Located on the arm, no associated systemic symptoms reported, Fitzpatrick phototype III, the patient considered this a rash, the contributor is male, the photograph was taken at an angle.
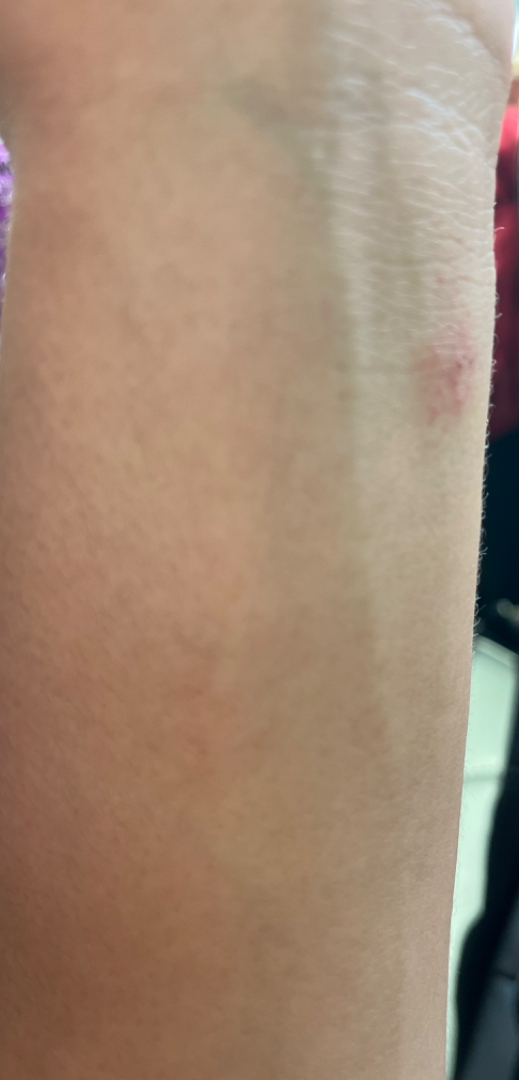On remote dermatologist review: Insect Bite (favored); Abrasion, scrape, or scab (possible); Allergic Contact Dermatitis (possible).